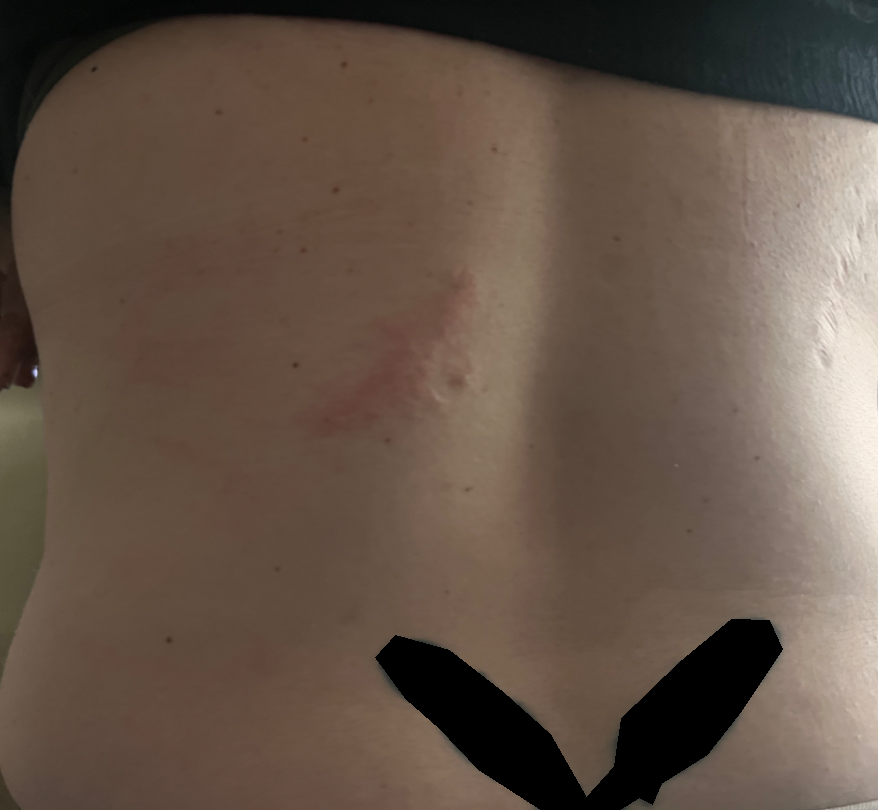{"assessment": "unable to determine", "duration": "less than one week", "body_site": "back of the torso", "patient_category": "a rash", "shot_type": "at a distance", "symptoms": ["pain", "itching", "burning", "enlargement"]}